The photograph was taken at an angle: 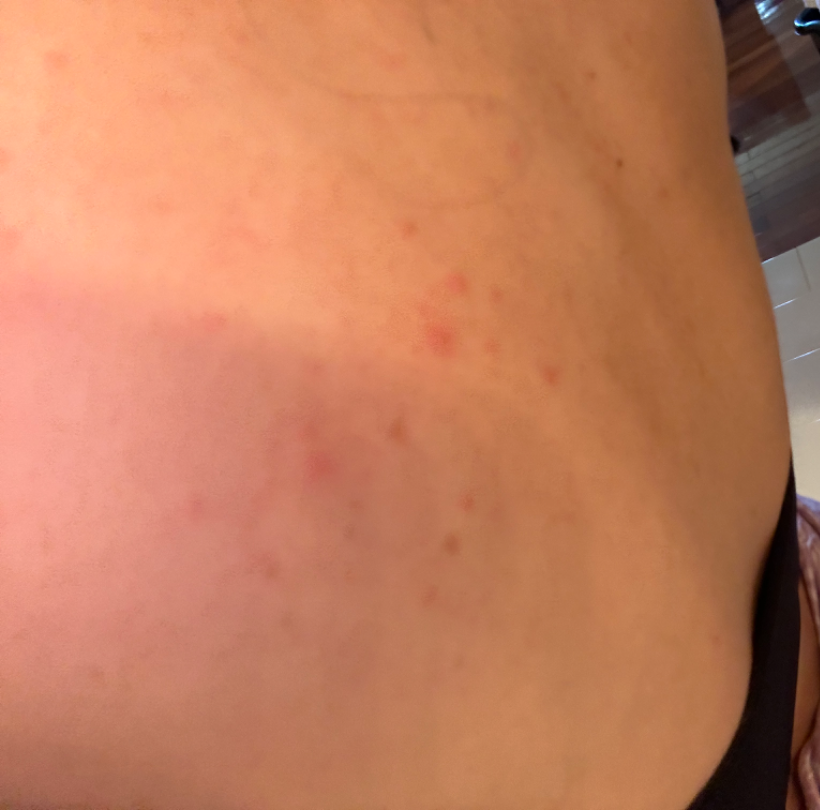Assessment: On remote review of the image: Allergic Contact Dermatitis (most likely); Acne (possible); Folliculitis (possible).